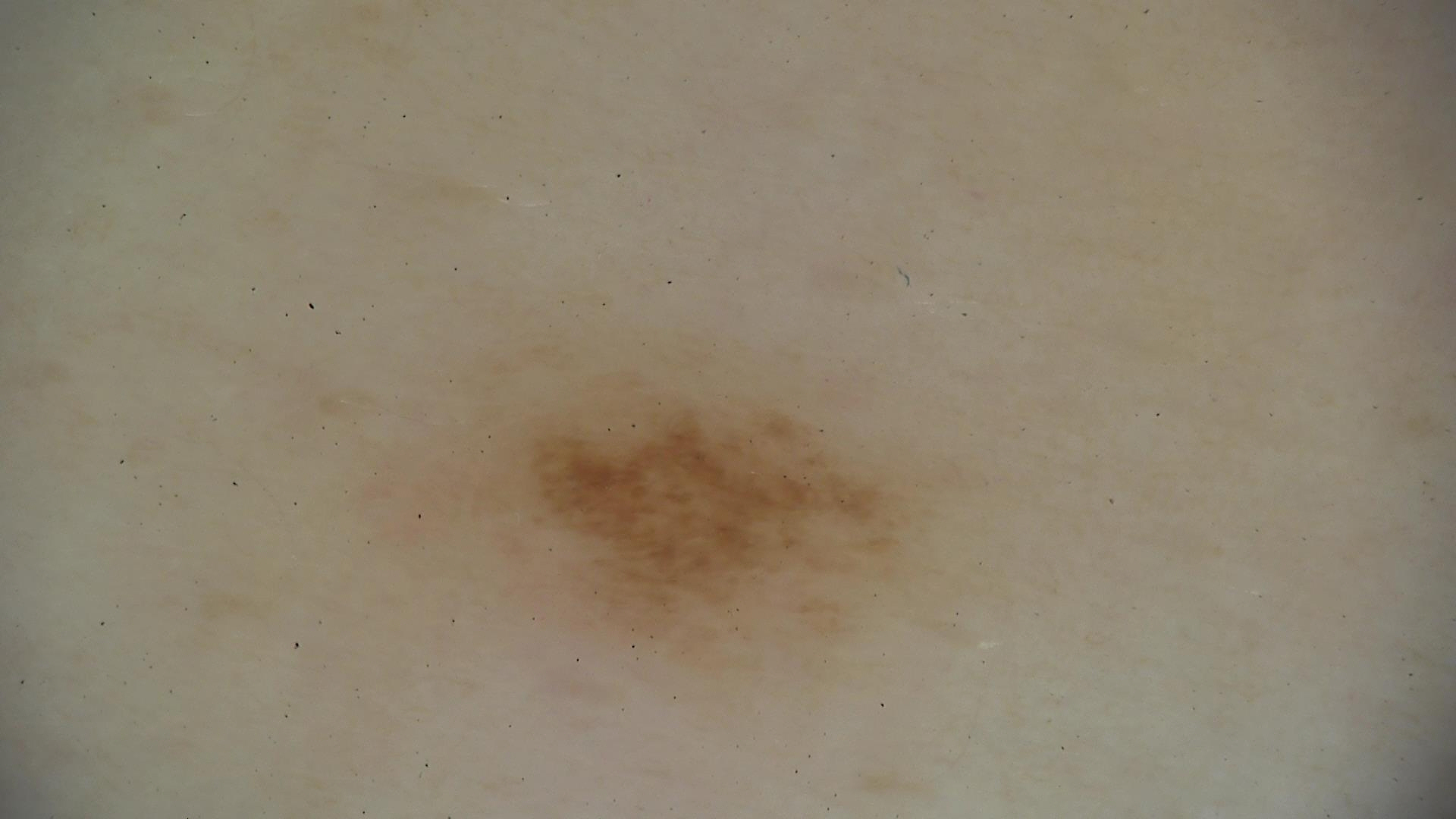Findings:
* modality: dermoscopy
* assessment: dysplastic junctional nevus (expert consensus)